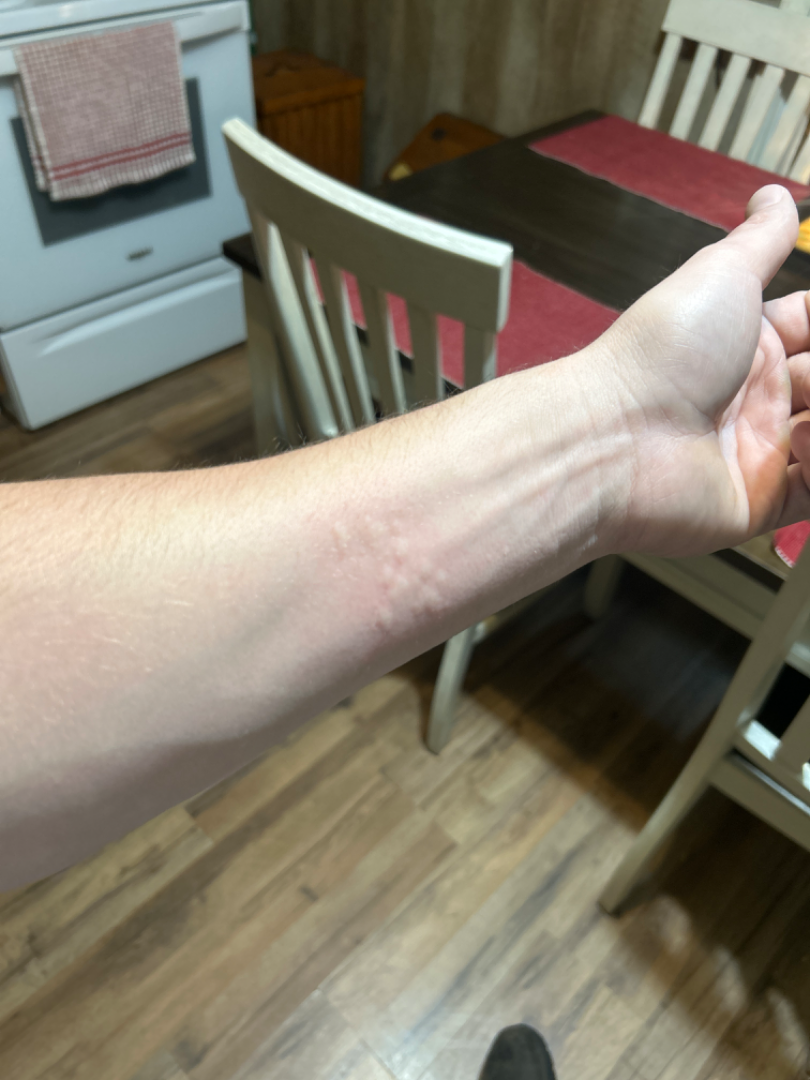Background: Skin tone: FST III. The photo was captured at a distance. Findings: On photographic review by a dermatologist, Urticaria (leading).